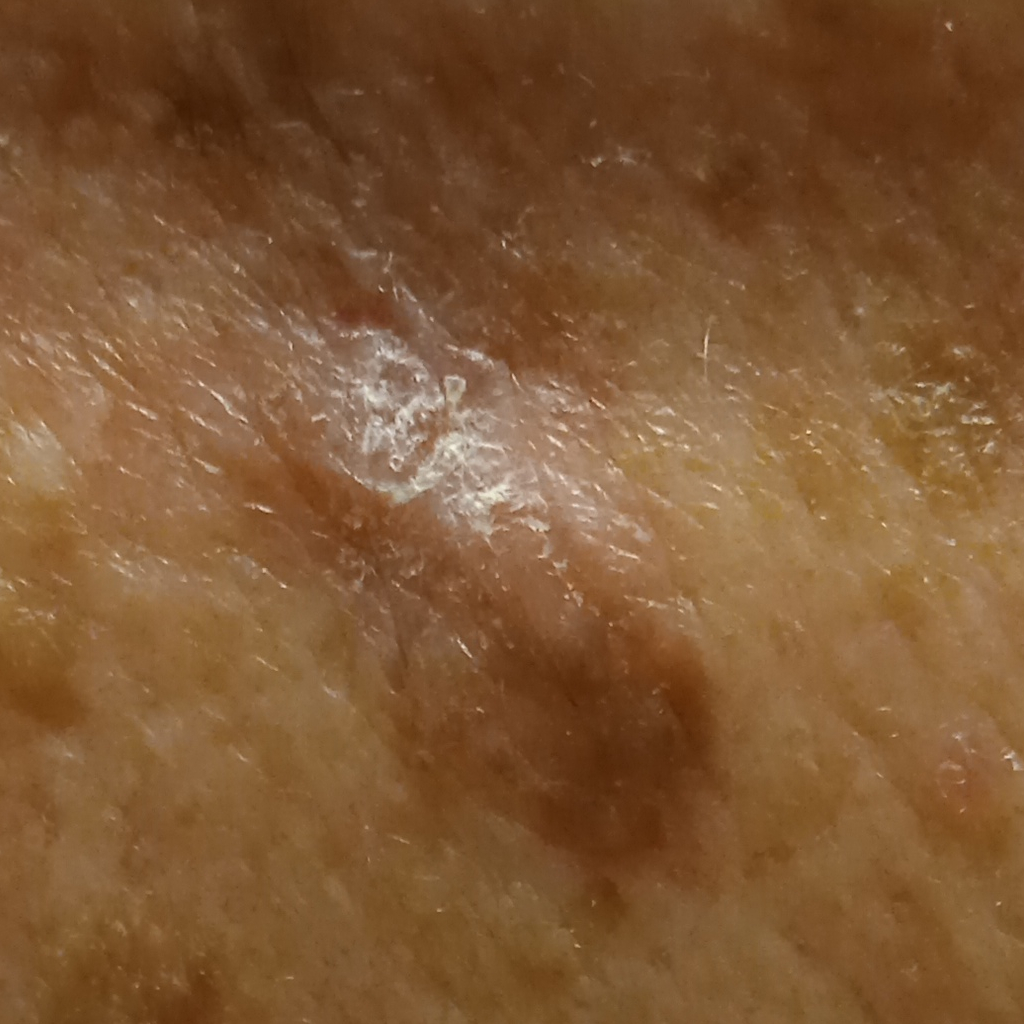Findings:
- subject: male, aged 62
- referral context: research study (no referral diagnosis)
- site: the back
- diameter: 13.8 mm
- diagnostic label: squamous cell carcinoma (dermatologist consensus)